A clinical close-up photograph of a skin lesion. The patient was assessed as Fitzpatrick skin type II:
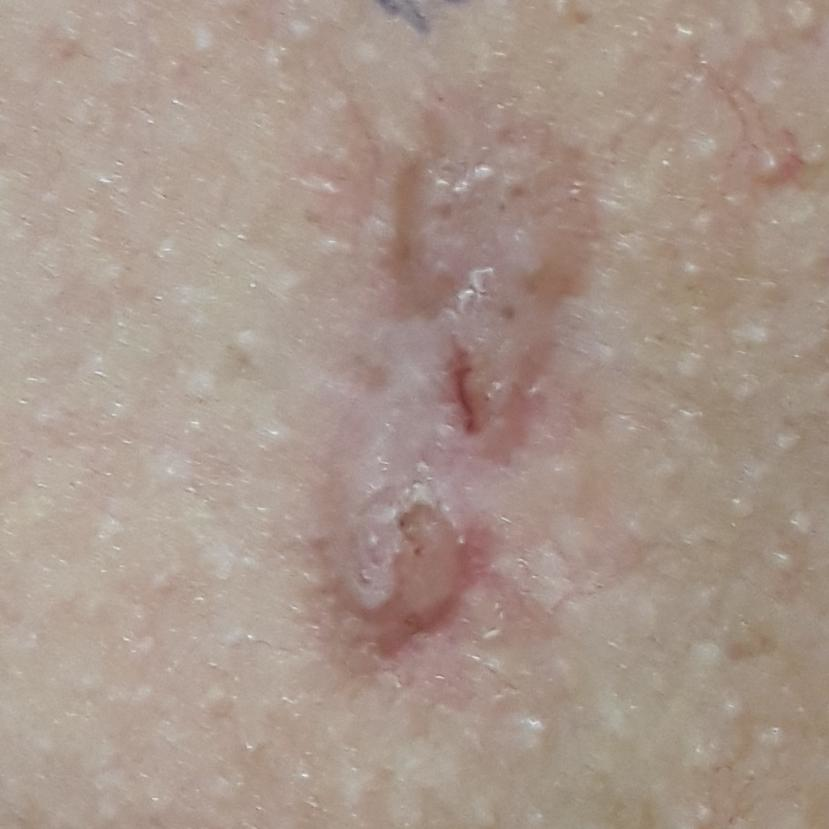The lesion is on the chest. The lesion measures 22 × 6 mm. The patient reports that the lesion itches, is elevated, and has grown. Histopathology confirmed a basal cell carcinoma.